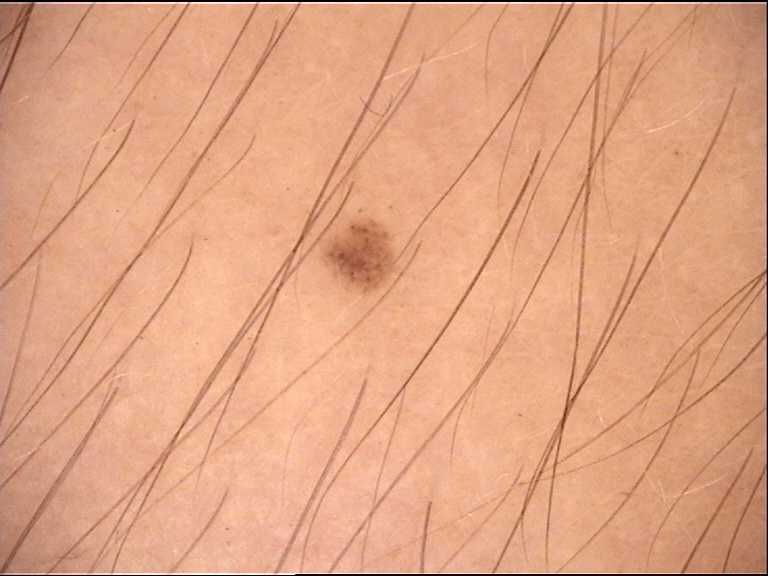Labeled as a junctional nevus.